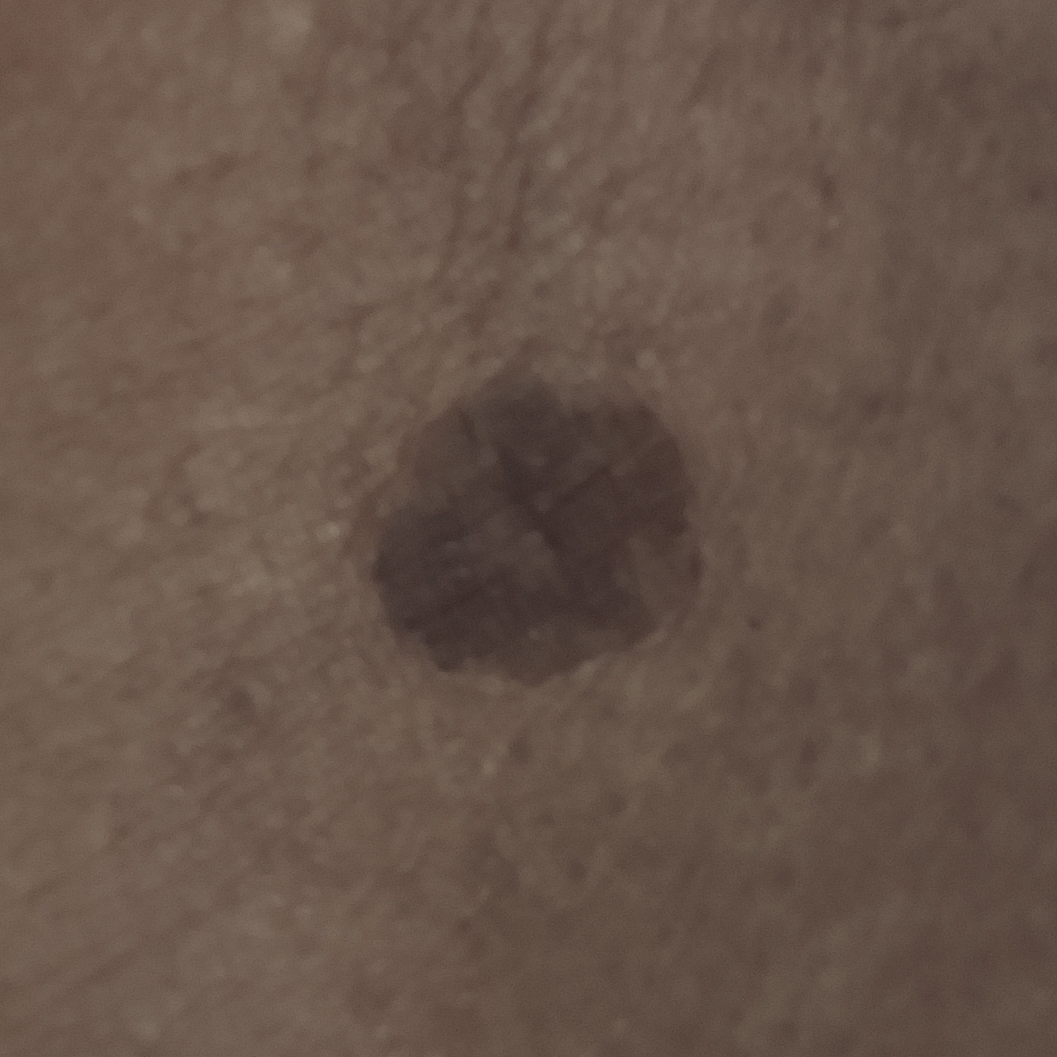Clinical context:
A clinical close-up photograph of a skin lesion. The lesion was found on a thigh.
Impression:
Consistent with a seborrheic keratosis.